Dermoscopy of a skin lesion: 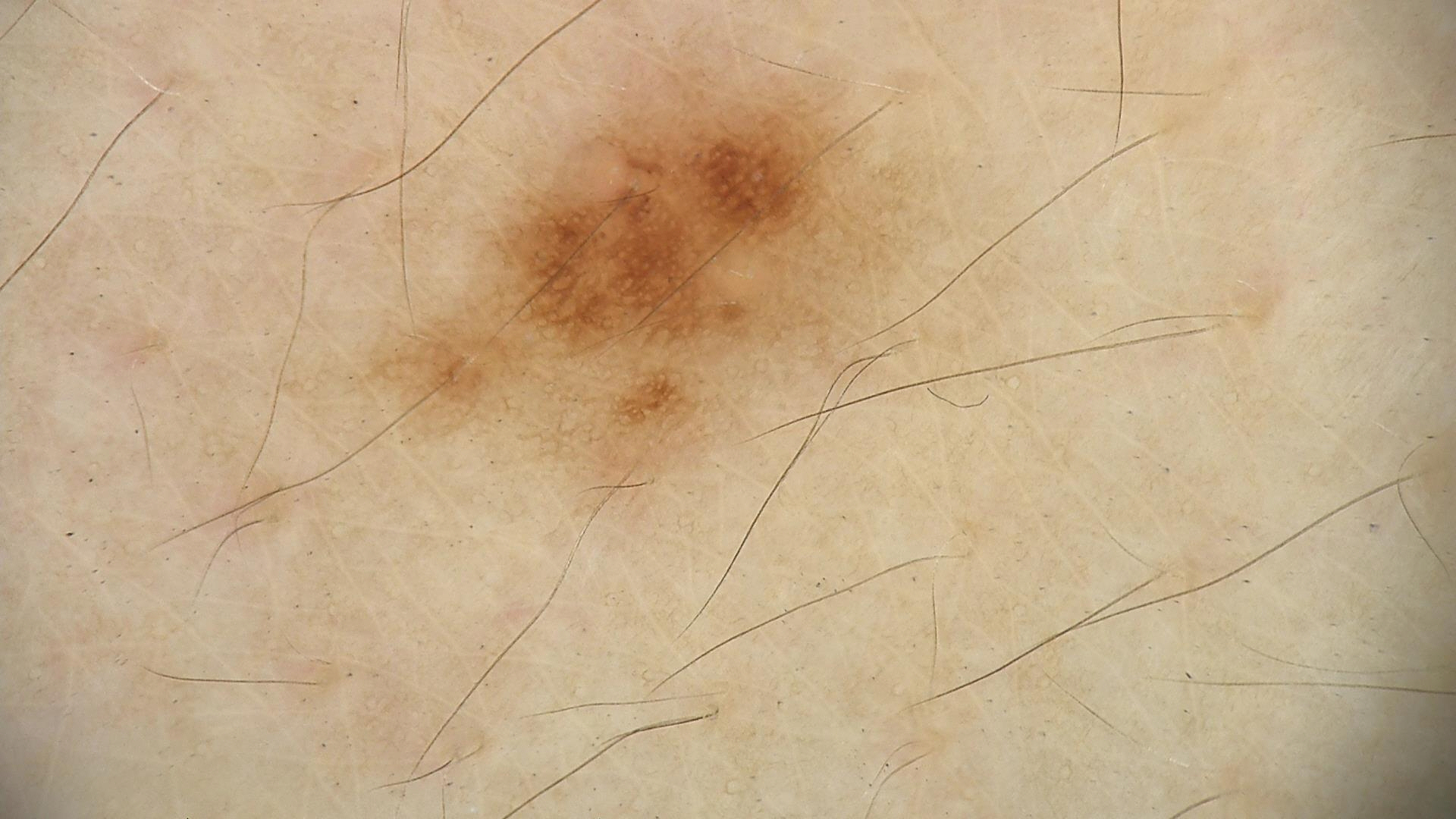diagnosis:
  name: dysplastic junctional nevus
  code: jd
  malignancy: benign
  super_class: melanocytic
  confirmation: expert consensus